Referred for assessment of suspected Bowen's disease · a clinical photograph showing a skin lesion · a male patient 83 years old — 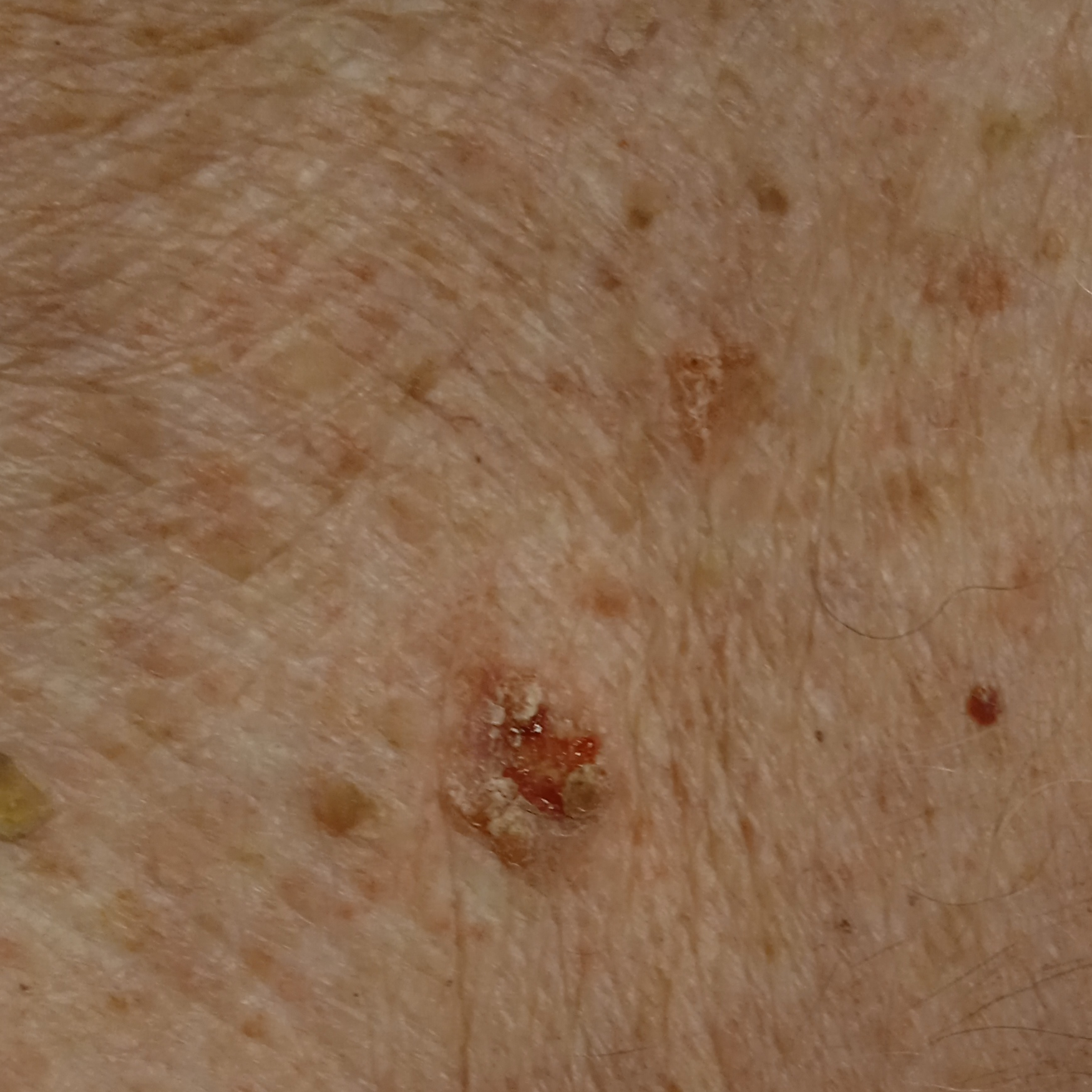Conclusion: The diagnostic impression was a squamous cell carcinoma.